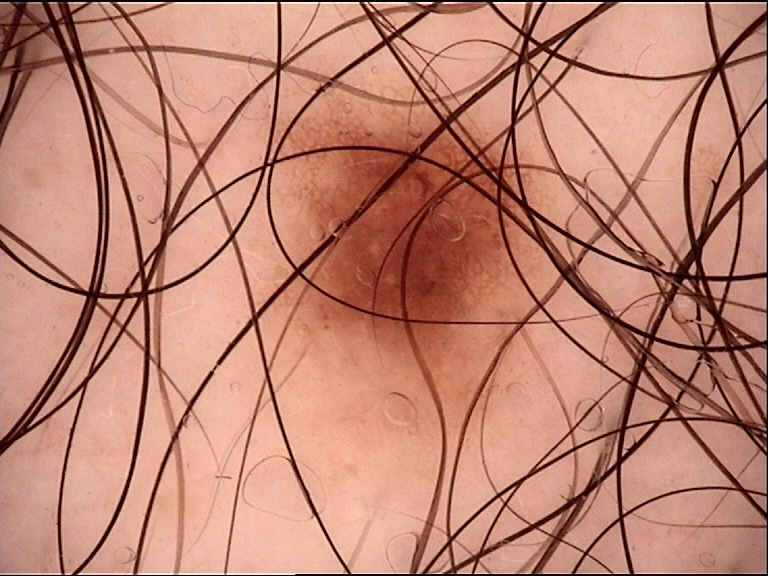Dermoscopy of a skin lesion.
Diagnosed as a benign lesion — a dysplastic junctional nevus.